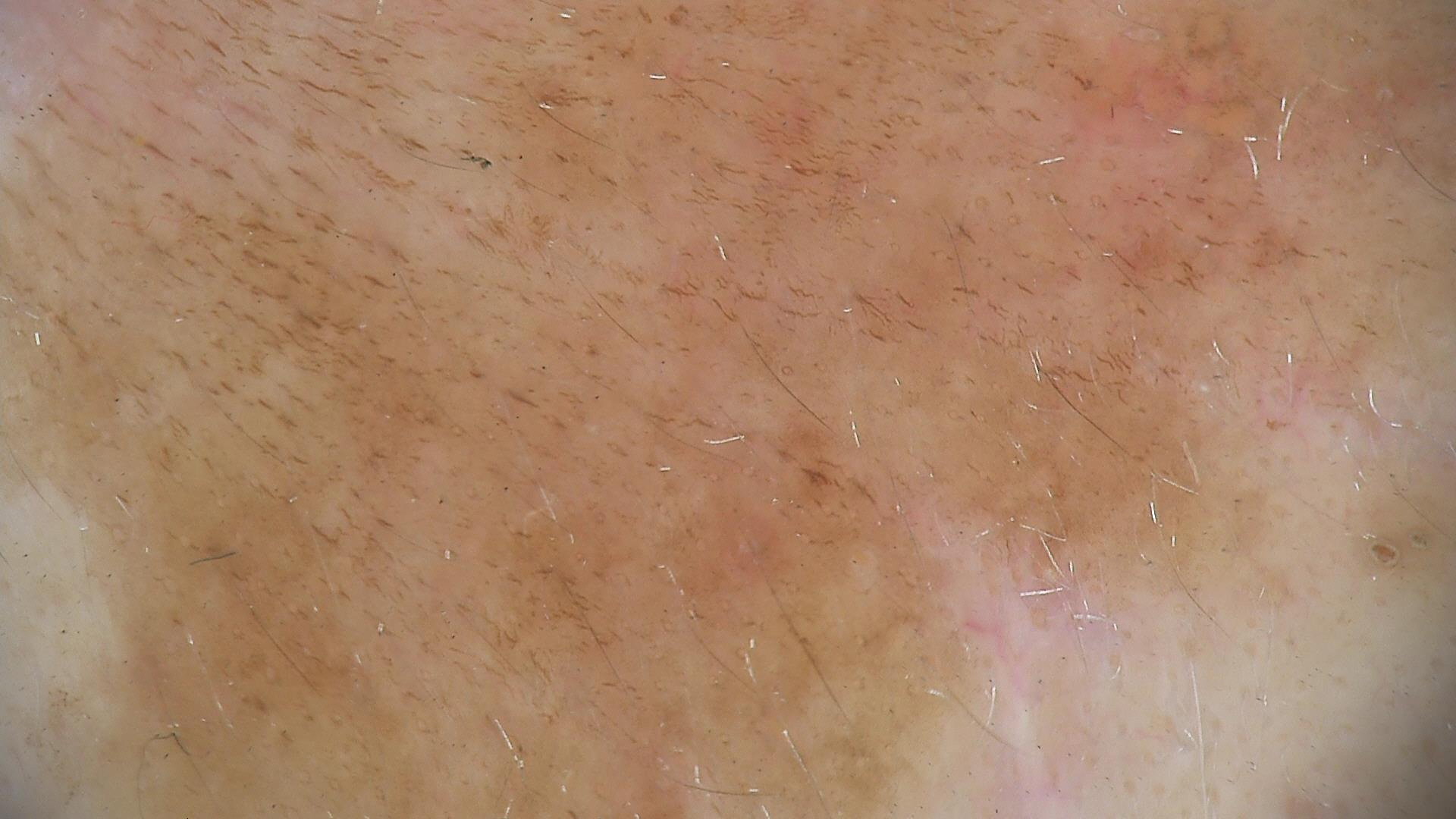{
  "diagnosis": {
    "name": "seborrheic keratosis",
    "code": "sk",
    "malignancy": "benign",
    "super_class": "non-melanocytic",
    "confirmation": "expert consensus"
  }
}